FST II. Contact-polarized dermoscopy of a skin lesion.
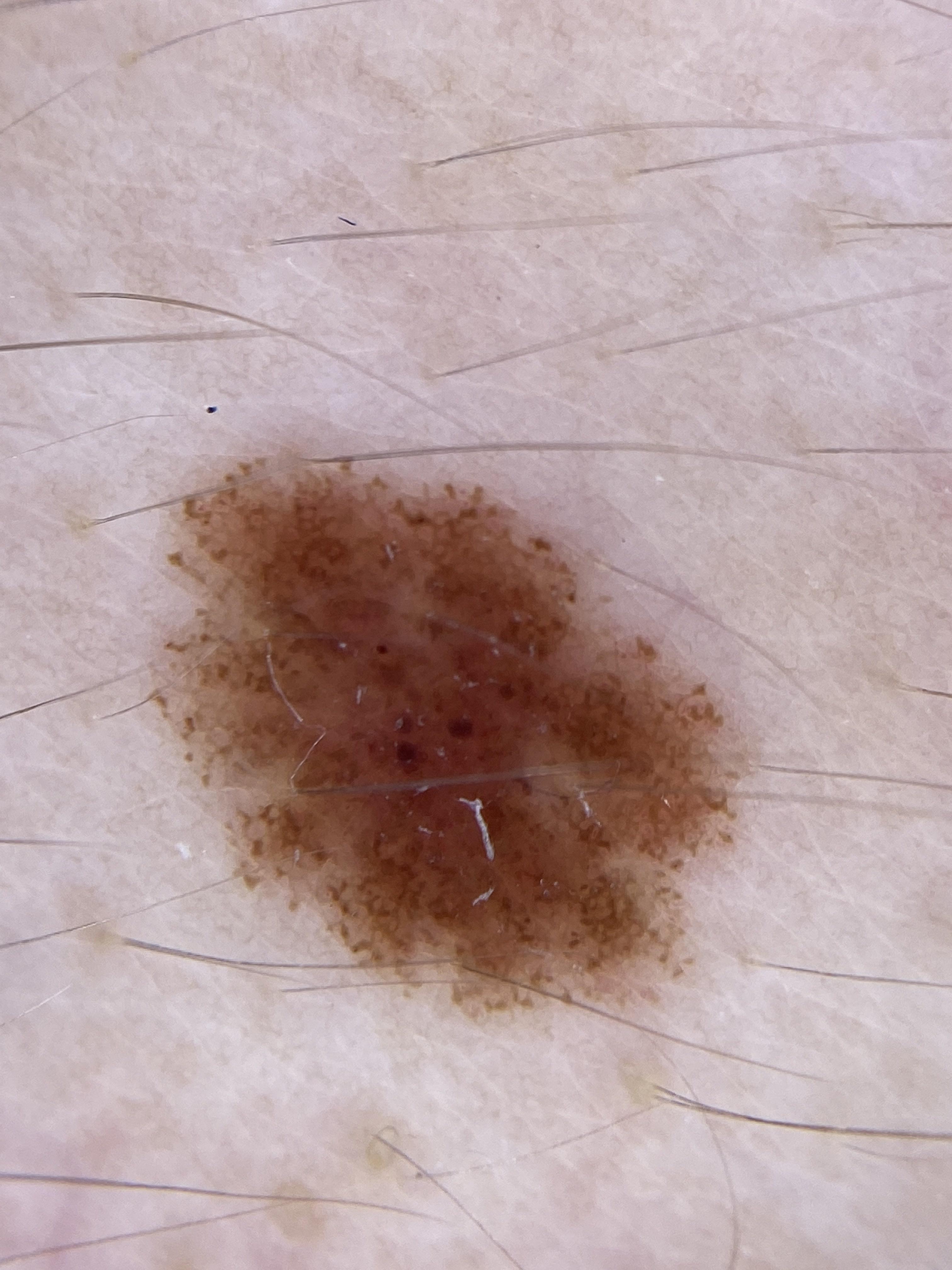Findings:
– diagnostic label — Nevus (biopsy-proven)